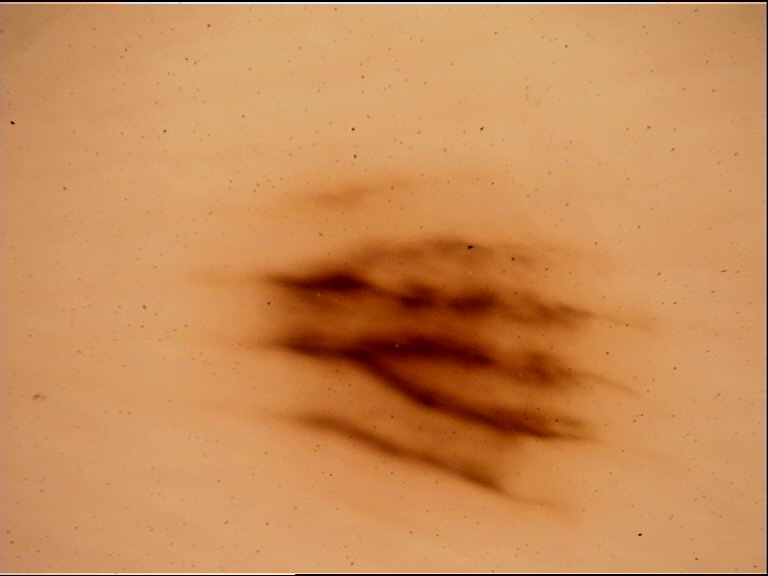A dermoscopic image of a skin lesion. The diagnosis was an acral junctional nevus.